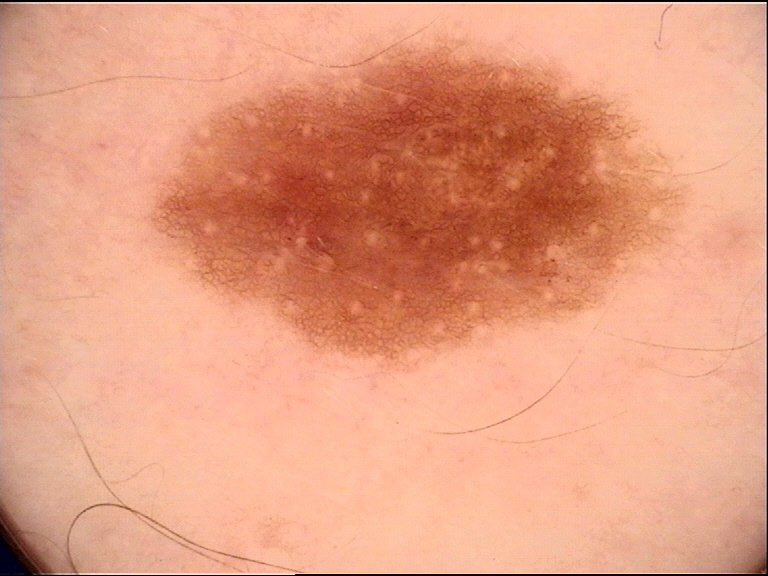diagnosis:
  name: dysplastic junctional nevus
  code: jd
  malignancy: benign
  super_class: melanocytic
  confirmation: expert consensus